Close-up view. The affected area is the arm and leg. Female contributor, age 40–49:
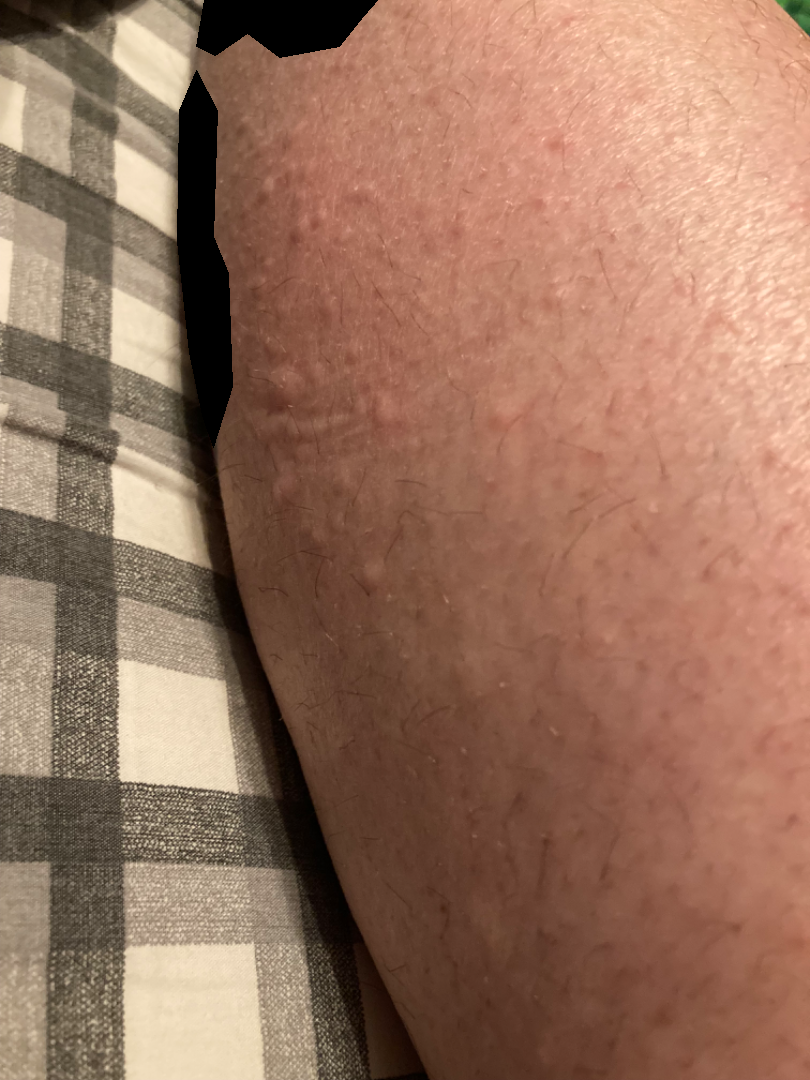lesion symptoms: bothersome appearance, enlargement and itching
patient describes the issue as: a rash
described texture: raised or bumpy
assessment: the favored diagnosis is Urticaria; also raised was Eczema; also consider Insect Bite